The subject is a male aged approximately 70. Dermoscopy of a skin lesion — 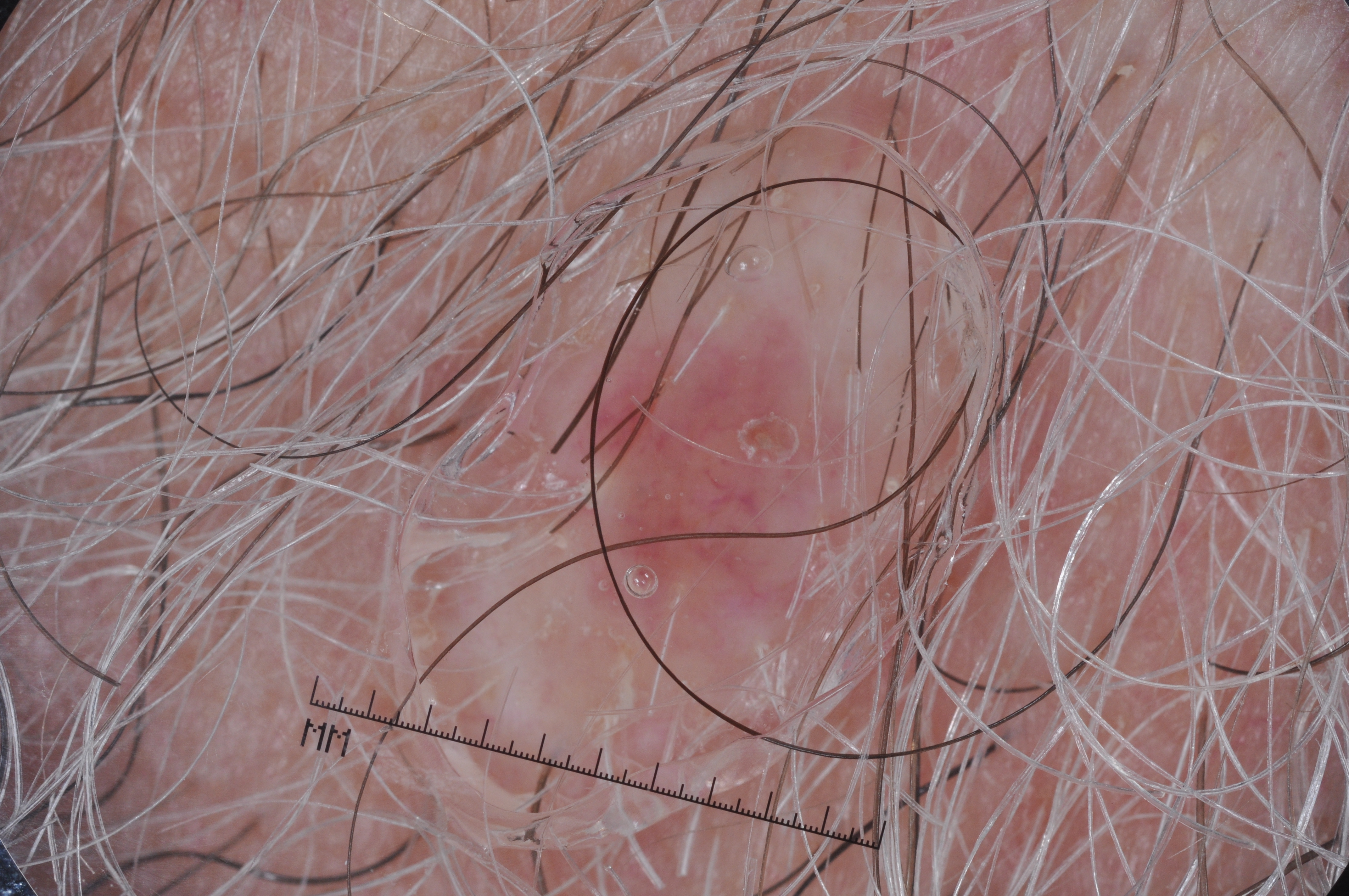absent dermoscopic features: negative network, milia-like cysts, streaks, and pigment network
size: ~5% of the field
location: <bbox>548, 329, 832, 595</bbox>
diagnostic label: a melanocytic nevus, a benign skin lesion